A macroscopic clinical photograph of a skin lesion; the patient says their skin reddens with sun exposure; a female subject 50 years of age; referred with a clinical suspicion of melanoma — 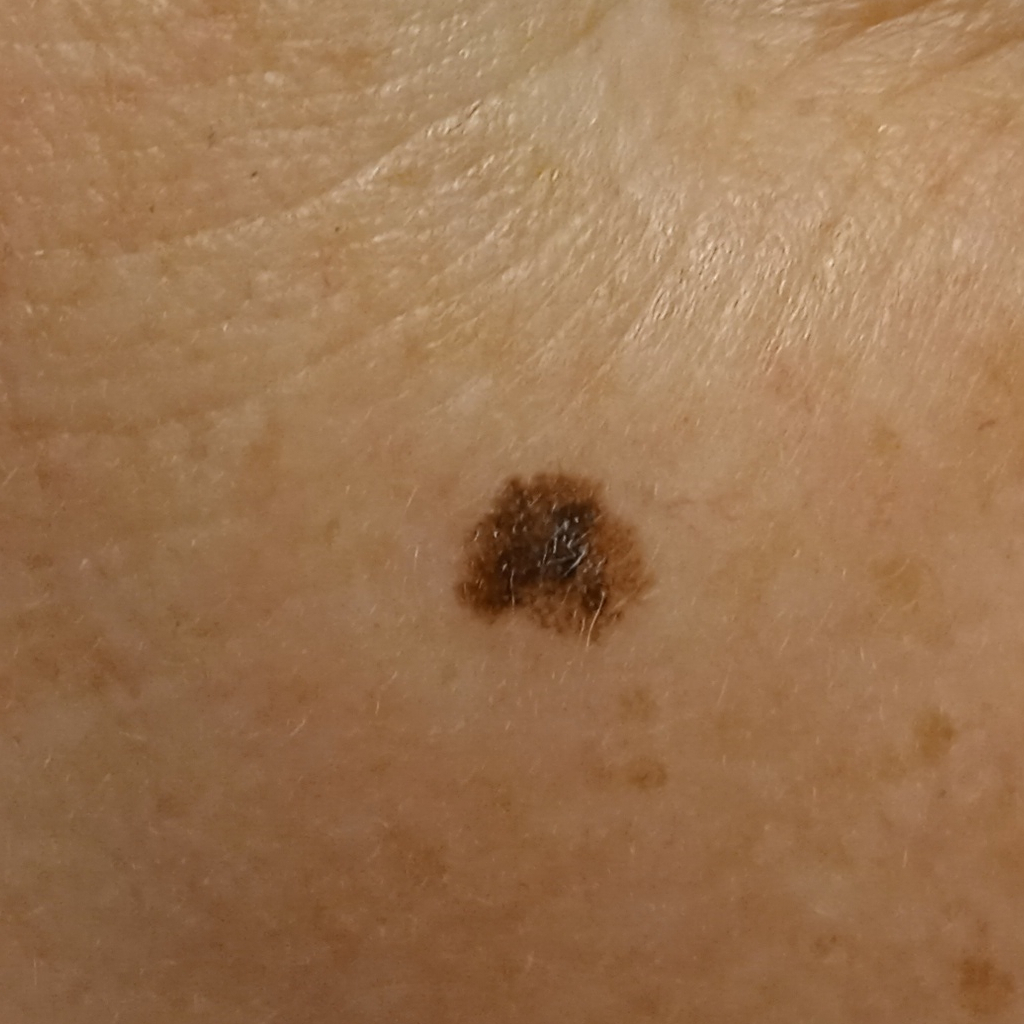Summary: The lesion measures approximately 7 mm. Conclusion: The biopsy diagnosis was a melanoma, following excision, with Breslow depth 0.4 mm.